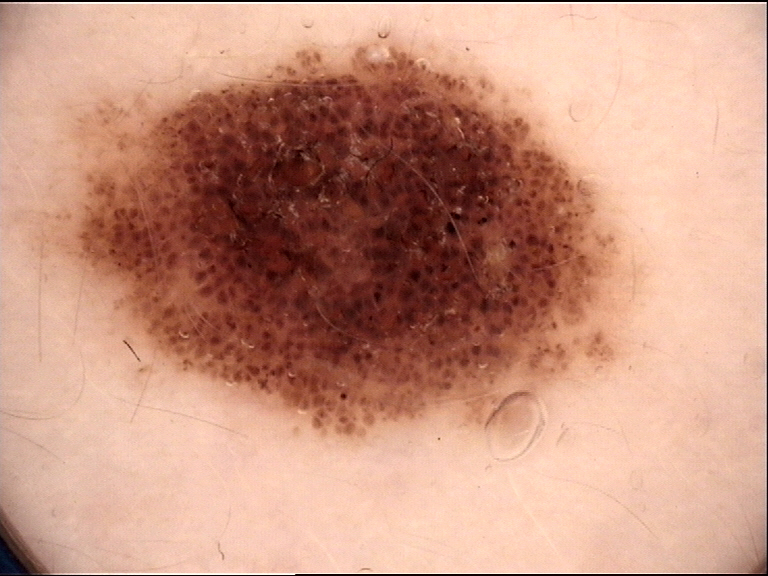A dermatoscopic image of a skin lesion. Classified as a dysplastic compound nevus.